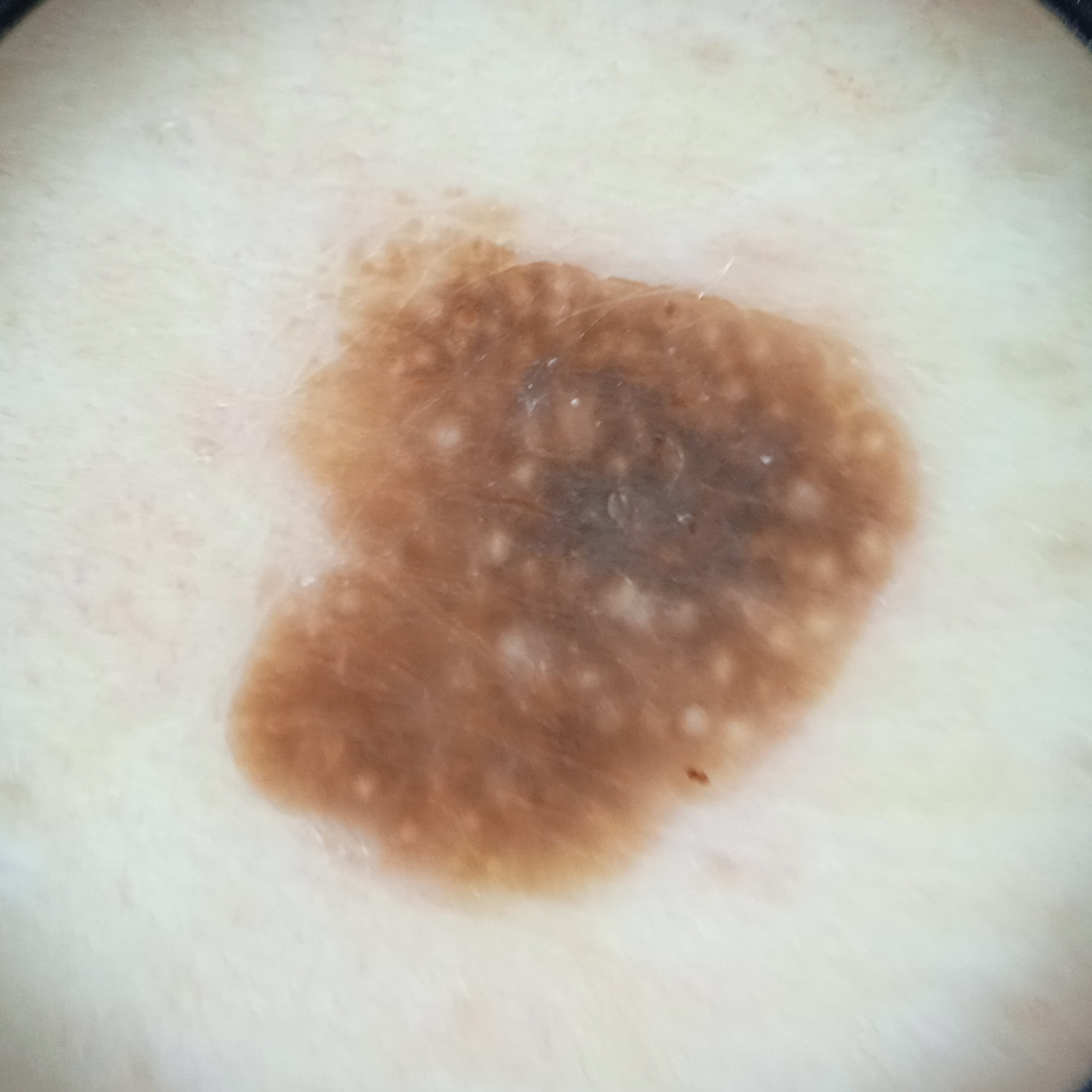Summary: A dermoscopic image of a skin lesion. A male patient 76 years of age. Acquired for a research image collection, with no referral diagnosis. Measuring roughly 8.6 mm. Impression: The lesion was assessed as a seborrheic keratosis.